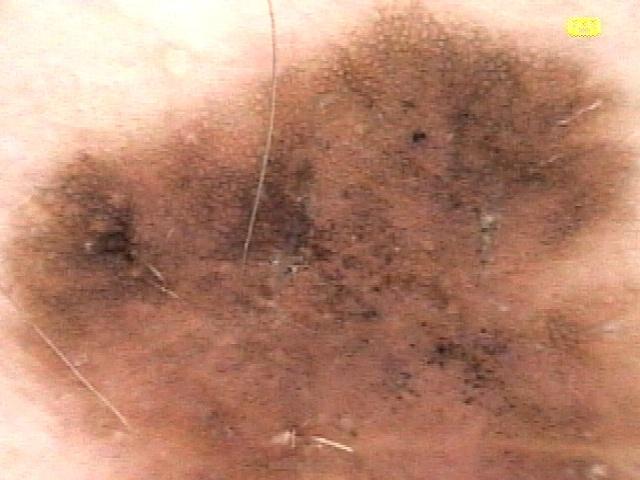patient = male, aged around 75; location = the trunk, specifically the posterior trunk; pathology = Melanoma (biopsy-proven).